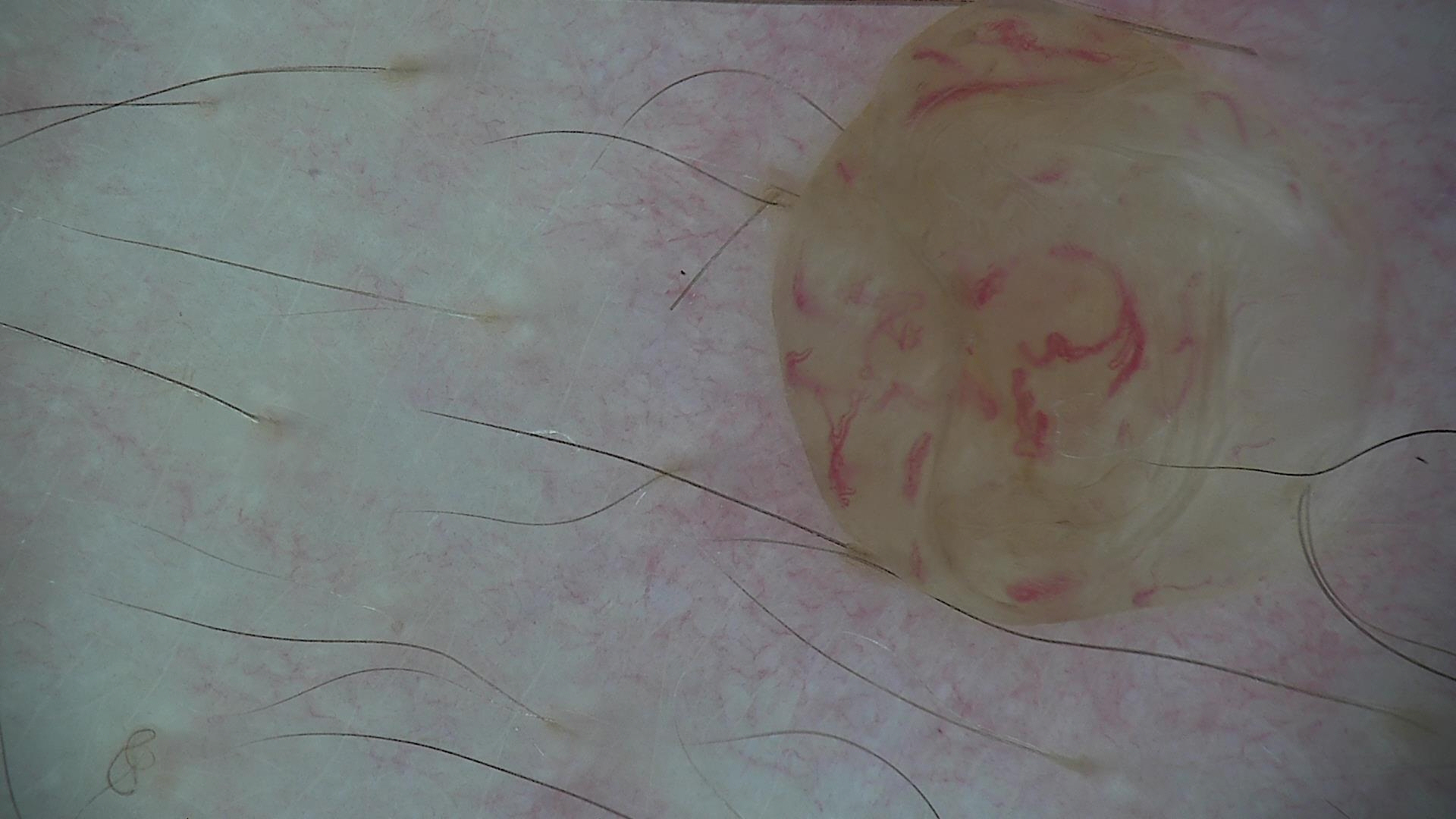Summary: A dermoscopic photograph of a skin lesion. Conclusion: The diagnostic label was a banal lesion — a dermal nevus.